The photograph is a close-up of the affected area — 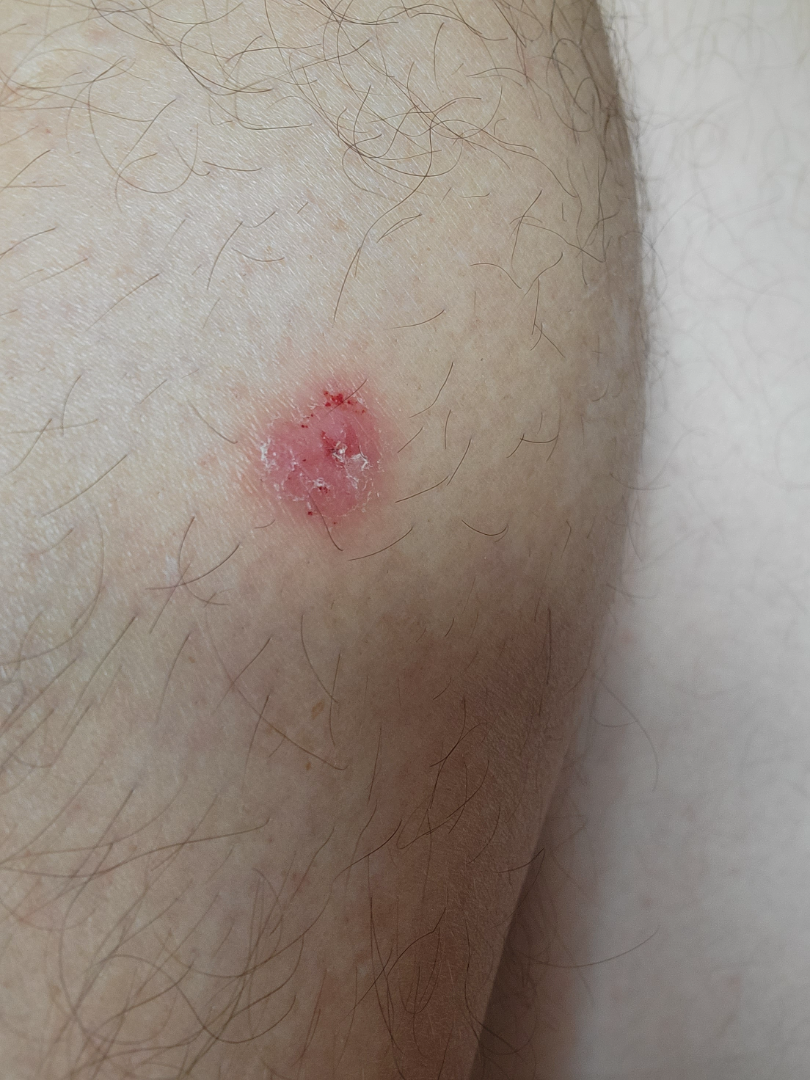Review: The reviewing clinician's impression was: the leading consideration is Eczema; possibly Psoriasis; the differential also includes SCC/SCCIS.